The head or neck is involved, the subject is a male aged 50–59, reported duration is more than one year, the patient considered this a rash, Fitzpatrick II, the lesion is described as rough or flaky, an image taken at an angle:
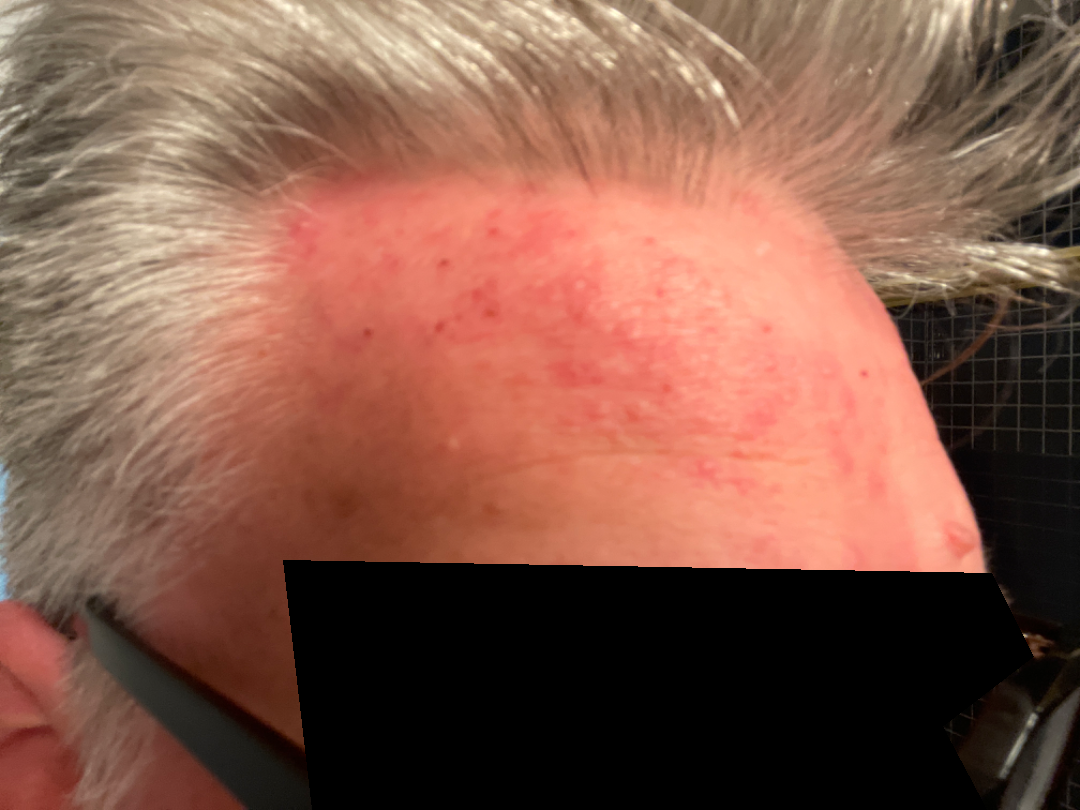{"differential": {"leading": ["Rosacea"]}}